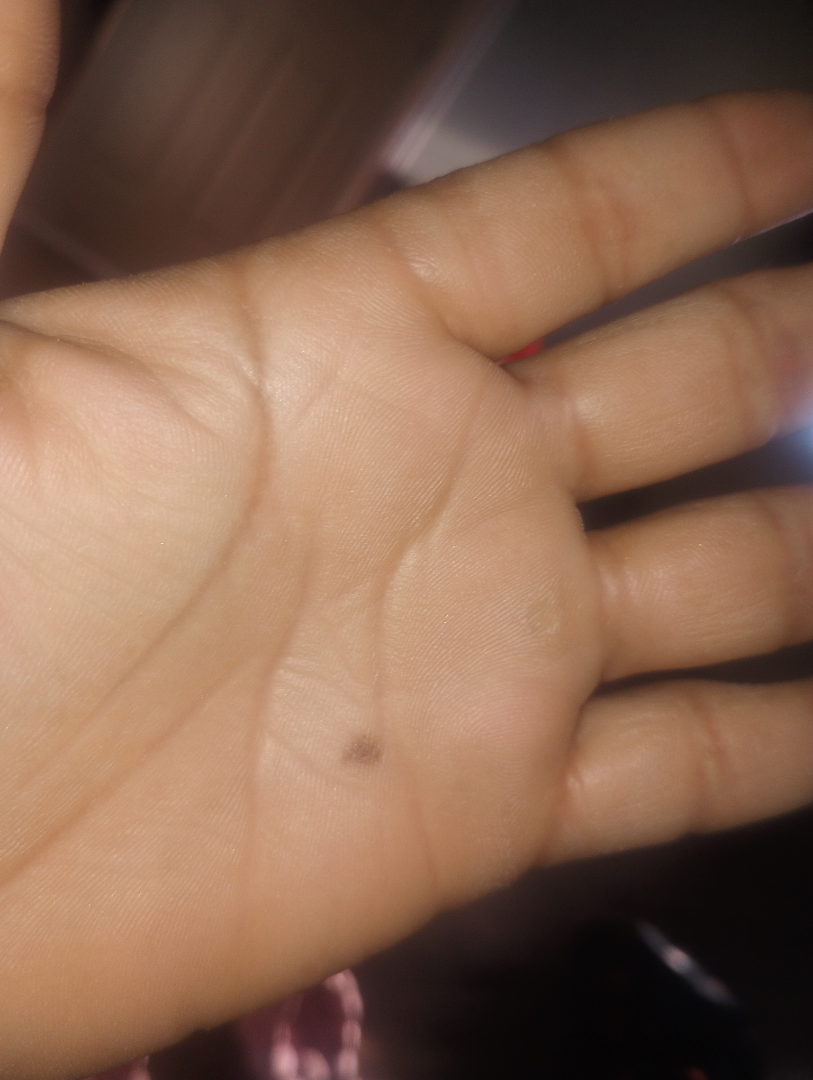assessment: not assessable
shot_type: close-up